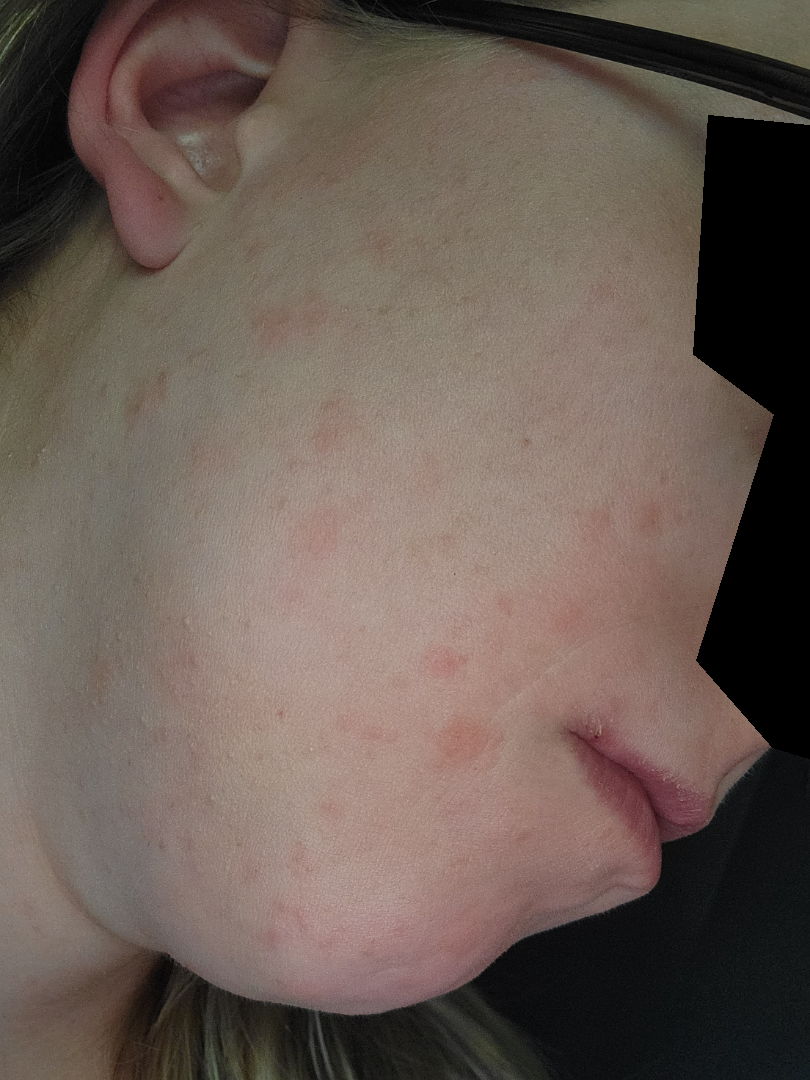The case was difficult to assess from the available photograph. Close-up view. Located on the head or neck.